A patient in their 70s · a clinical photograph of a skin lesion: 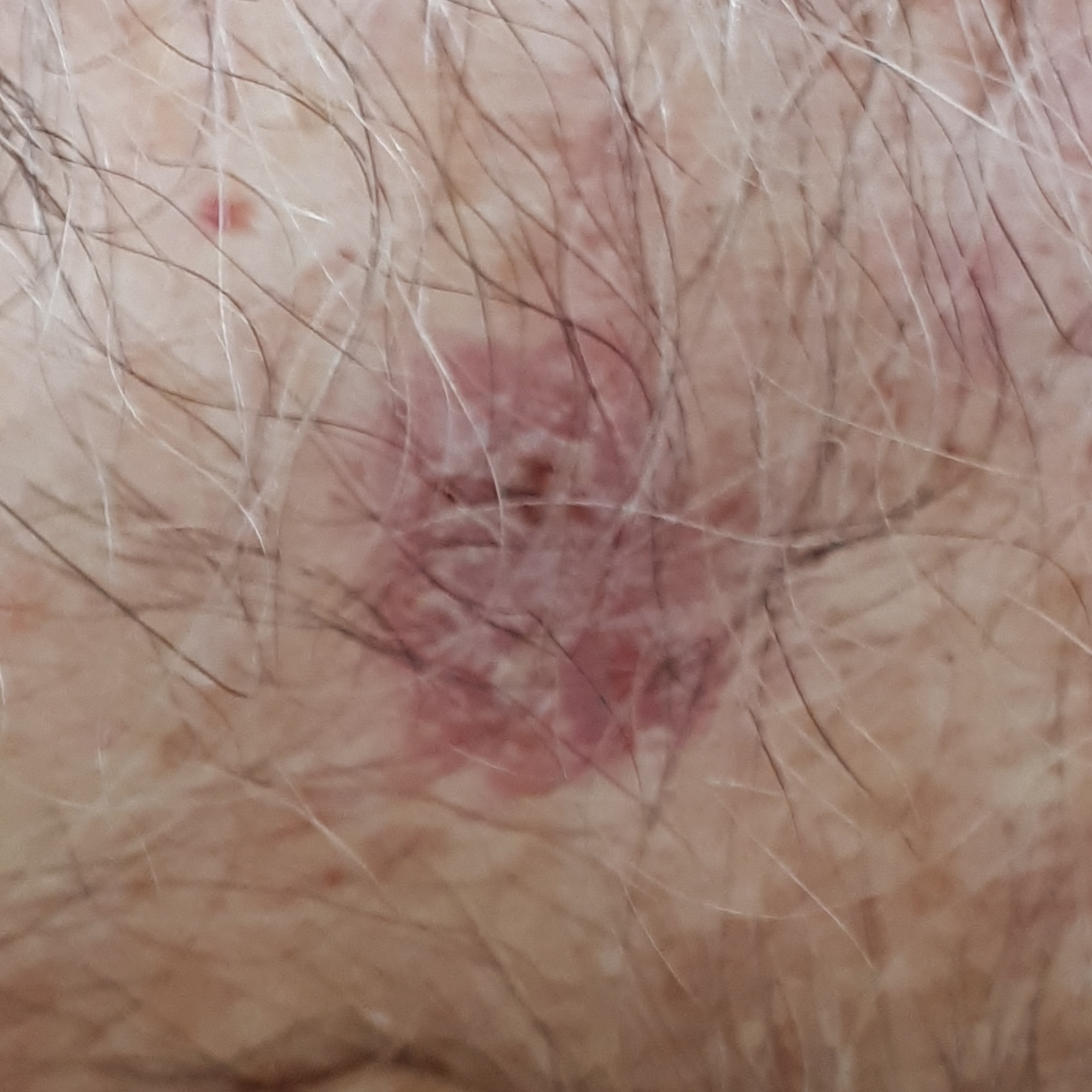patient-reported symptoms=itching
impression=actinic keratosis (clinical consensus)